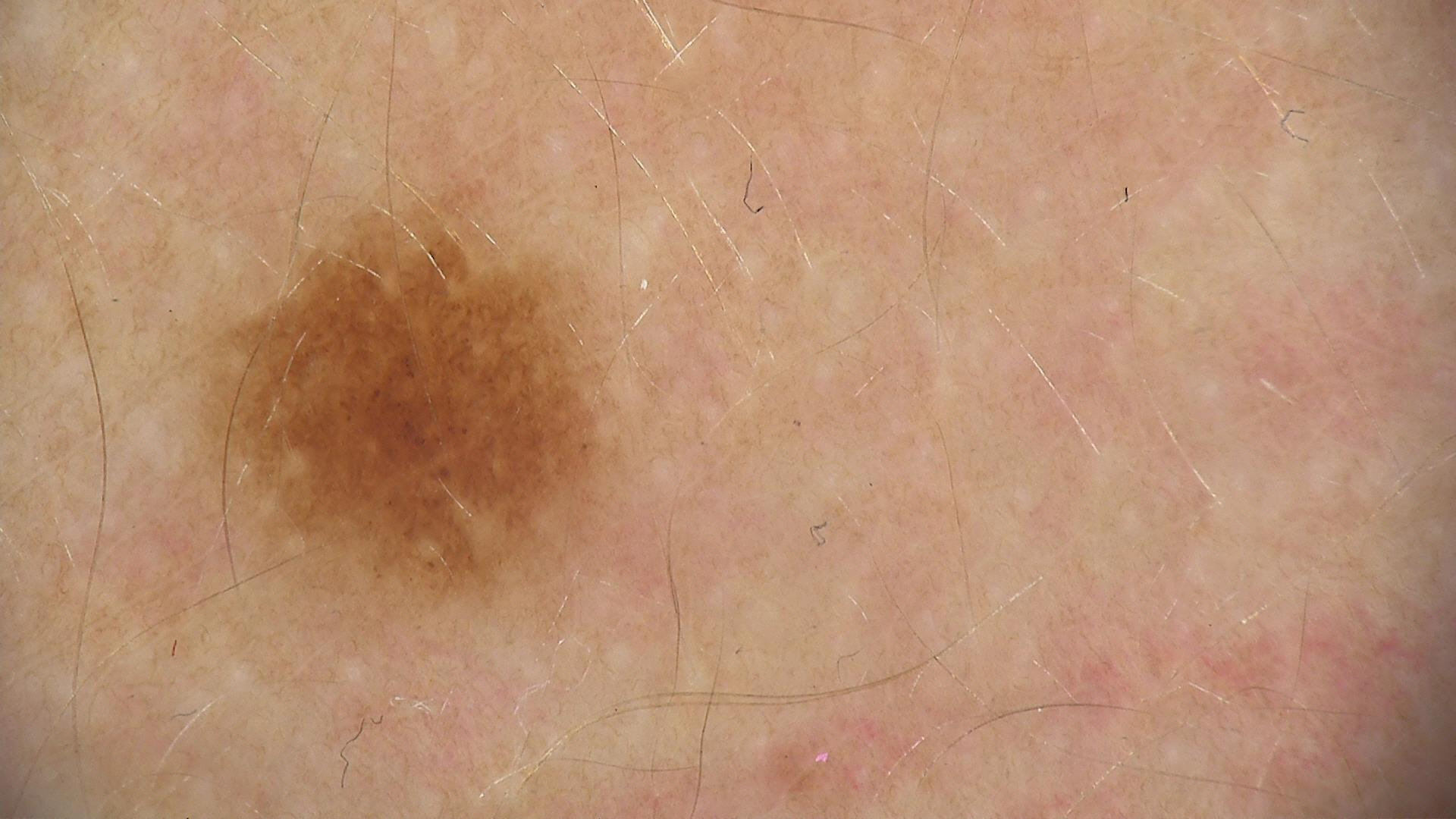{"image": "dermoscopy", "diagnosis": {"name": "dysplastic junctional nevus", "code": "jd", "malignancy": "benign", "super_class": "melanocytic", "confirmation": "expert consensus"}}